The lesion involves the front of the torso, back of the torso, leg and head or neck · the photograph is a close-up of the affected area — 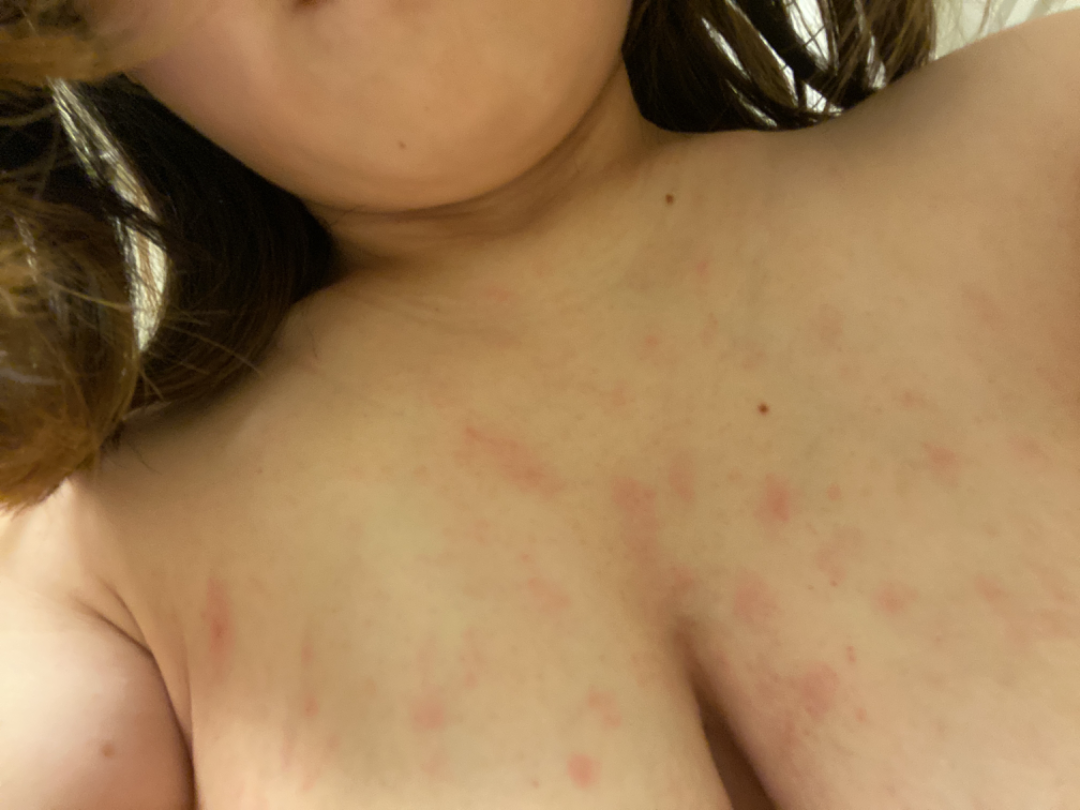Notes:
- differential · single-reviewer assessment: Drug Rash, Pityriasis rosea and Insect Bite were each considered, in no particular order